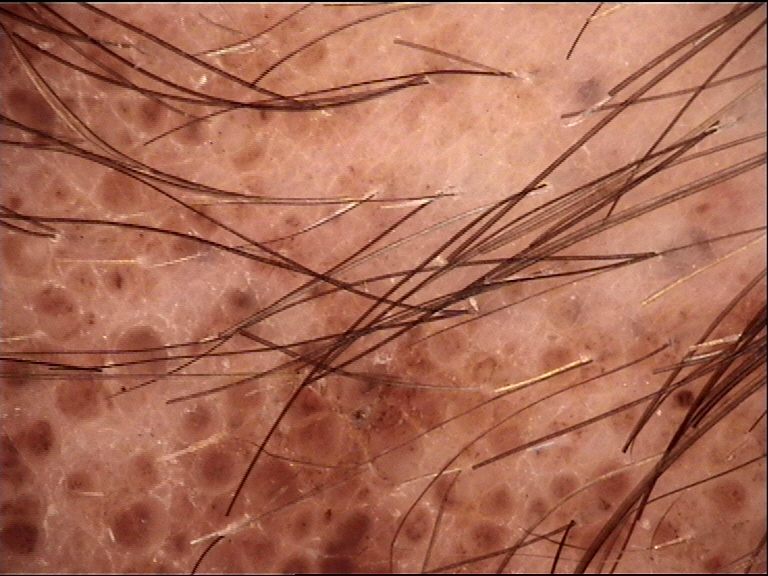Q: What kind of image is this?
A: dermoscopy
Q: What is the lesion category?
A: banal
Q: What was the diagnostic impression?
A: congenital compound nevus (expert consensus)